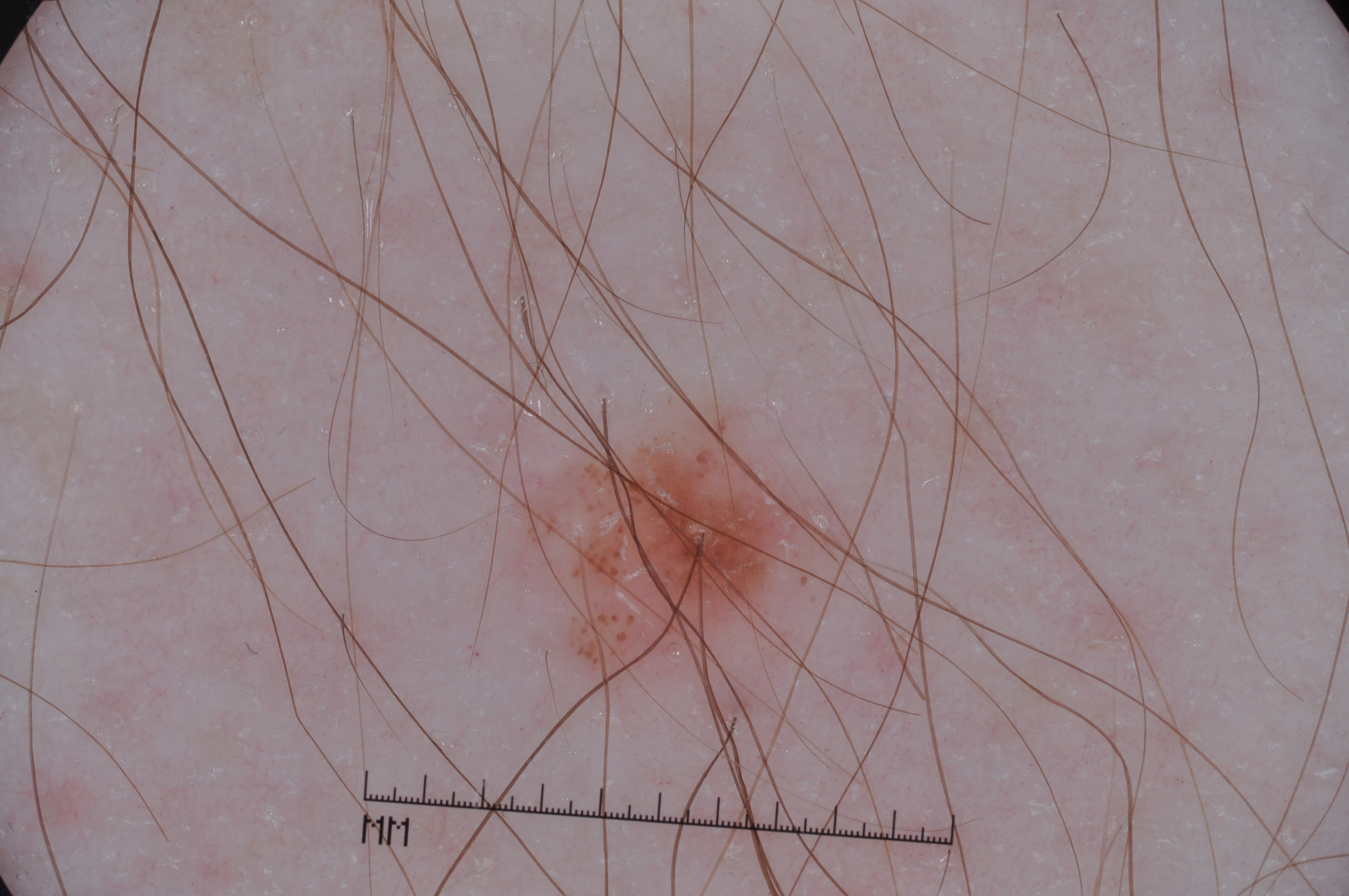Notes:
– imaging — dermoscopy
– subject — male, aged around 25
– absent dermoscopic findings — streaks, negative network, pigment network, and milia-like cysts
– lesion size — small
– lesion bbox — bbox=[506, 406, 843, 679]
– diagnostic label — a melanocytic nevus, a benign skin lesion